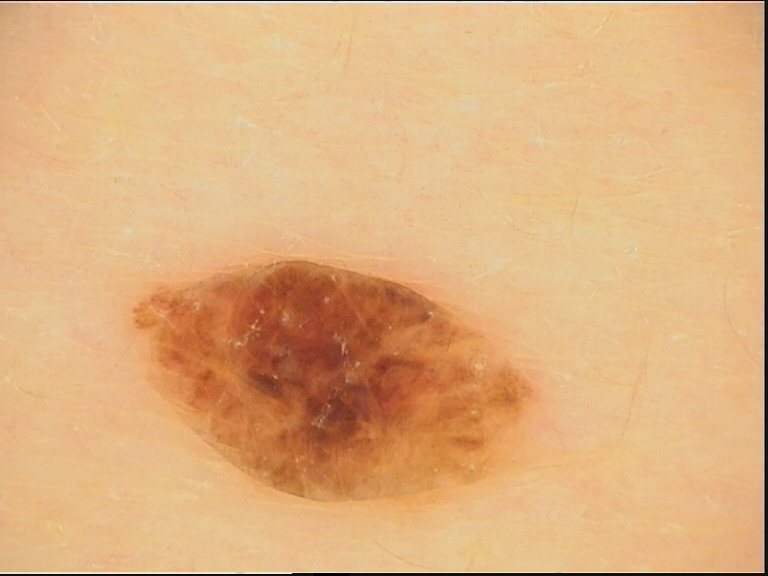Dermoscopy of a skin lesion.
The diagnostic label was a compound nevus.